The photograph is a close-up of the affected area. Male subject, age 18–29. FST II; lay graders estimated 2 on the Monk Skin Tone. The affected area is the top or side of the foot. Symptoms reported: itching. The contributor reports the condition has been present for about one day.
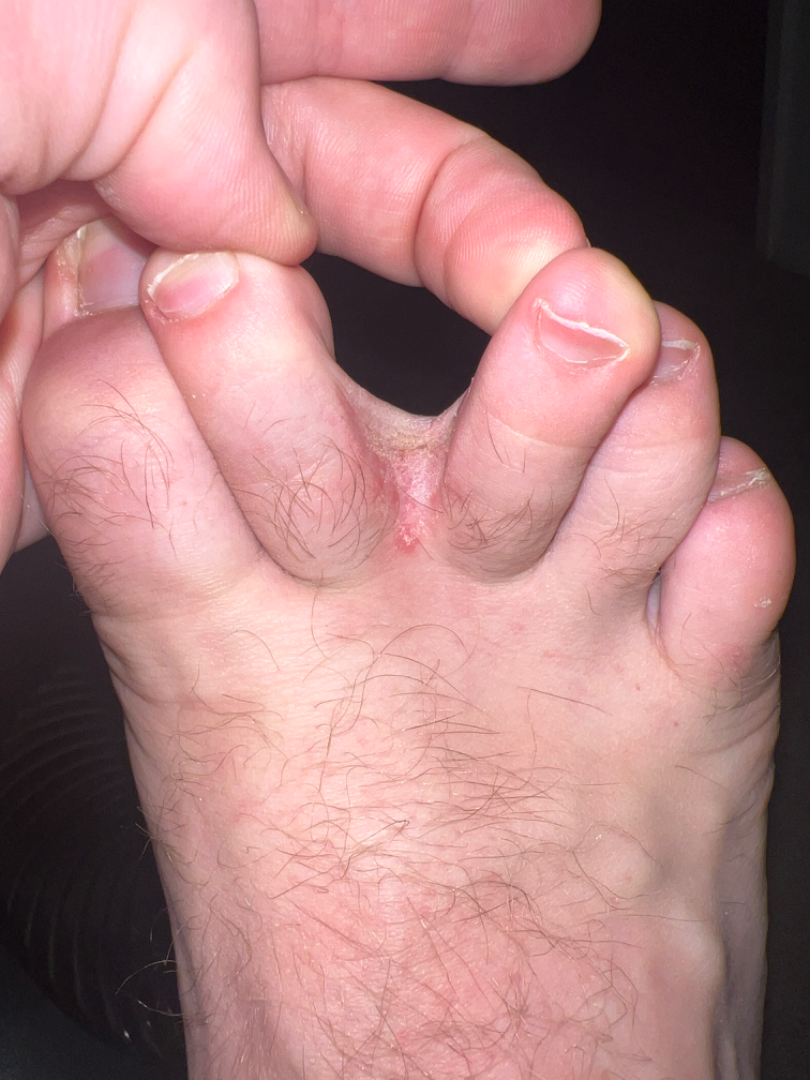{
  "differential": {
    "leading": [
      "Tinea"
    ],
    "considered": [
      "Candida"
    ],
    "unlikely": [
      "Eczema",
      "Skin and soft tissue atypical mycobacterial infection"
    ]
  }
}